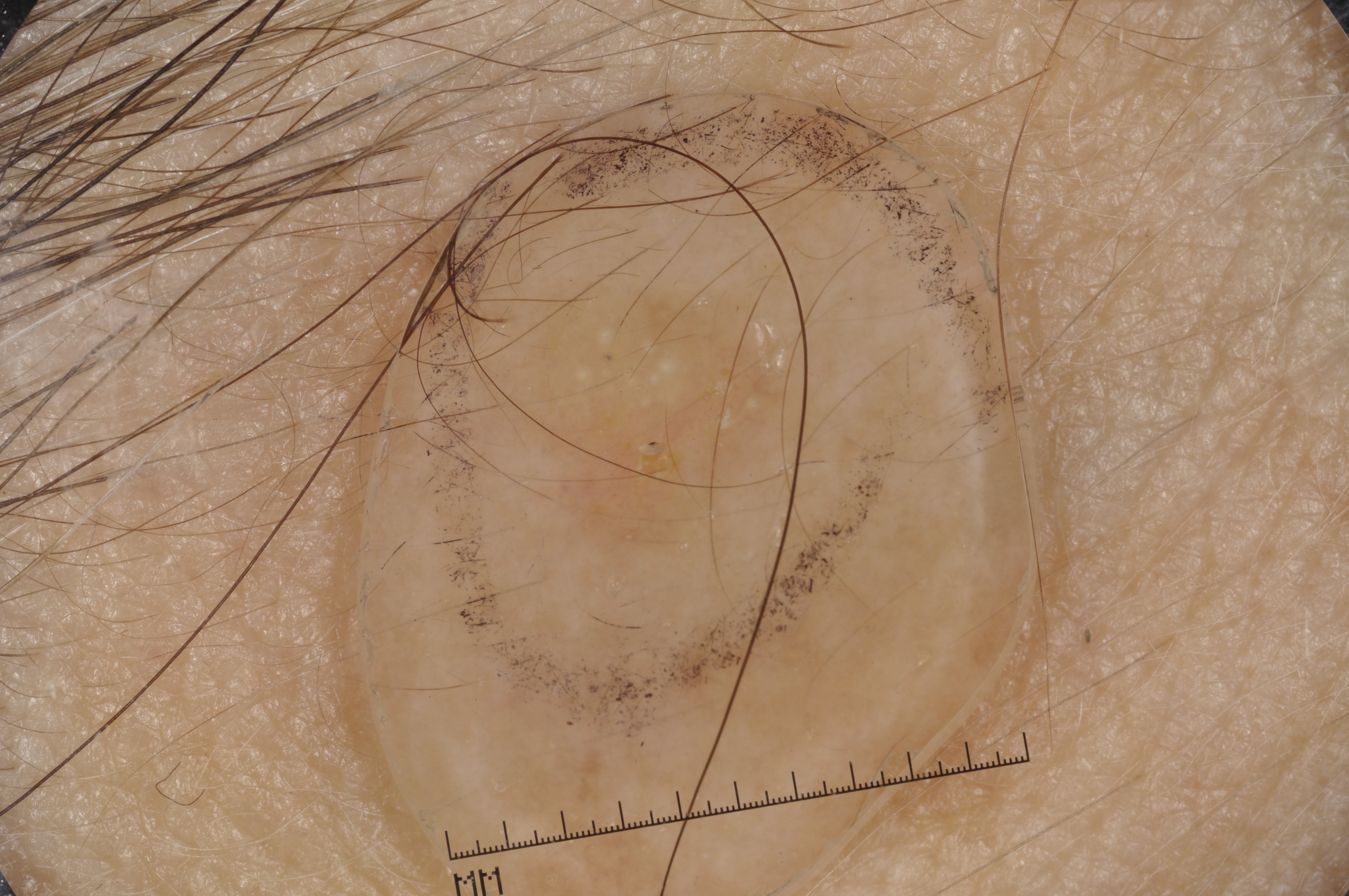A dermoscopic view of a skin lesion.
A female subject roughly 55 years of age.
With coordinates (x1, y1, x2, y2), the visible lesion spans <box>514, 255, 811, 567</box>.
On dermoscopy, the lesion shows milia-like cysts.
The lesion covers approximately 6% of the dermoscopic field.
The lesion was assessed as a seborrheic keratosis, a benign lesion.